A dermoscopic image of a skin lesion; a female subject, about 25 years old: 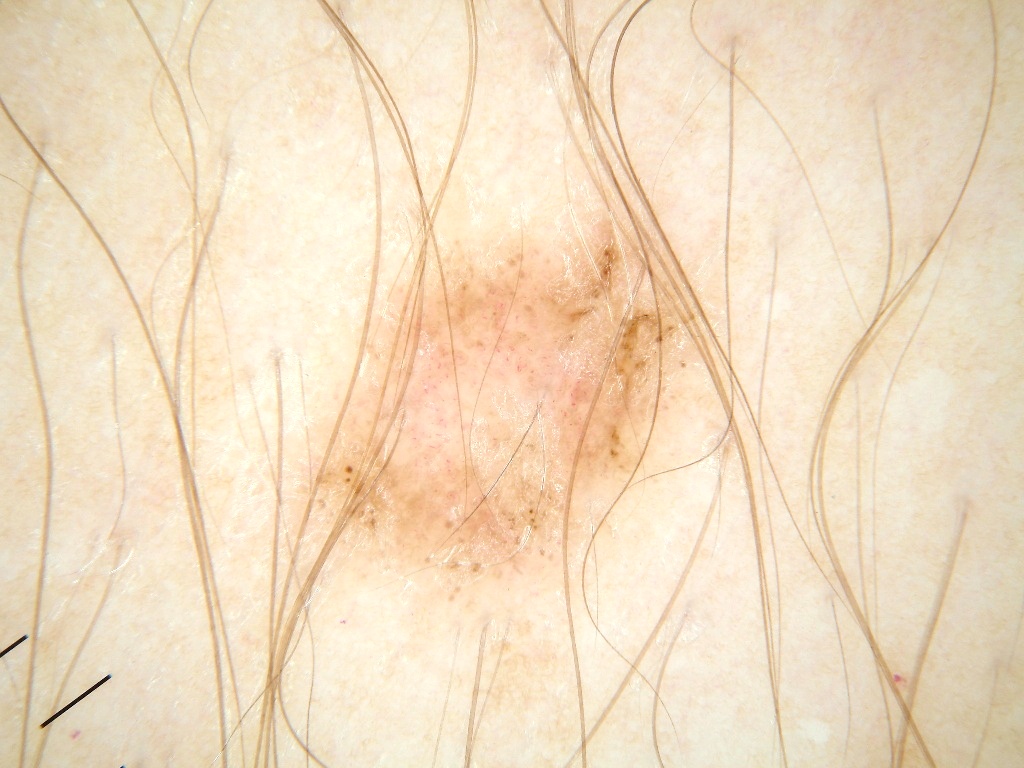dermoscopic_features:
  present:
    - globules
  absent:
    - milia-like cysts
    - negative network
    - pigment network
    - streaks
lesion_location:
  bbox_xyxy:
    - 296
    - 197
    - 726
    - 607
diagnosis:
  name: melanoma
  malignancy: malignant
  lineage: melanocytic
  provenance: histopathology